A dermoscopic photograph of a skin lesion.
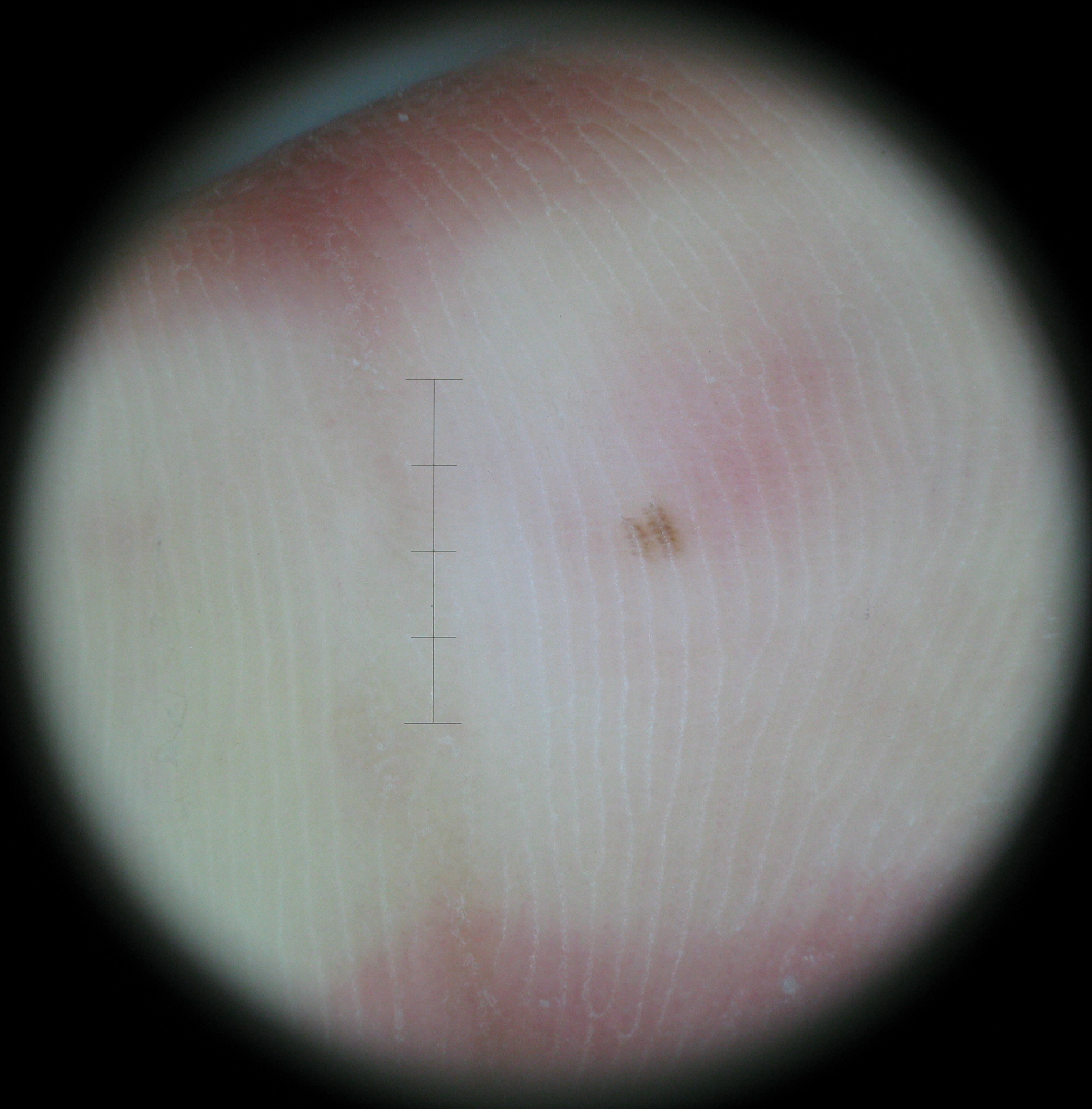Summary: The morphology is that of a banal lesion. Impression: Labeled as an acral junctional nevus.